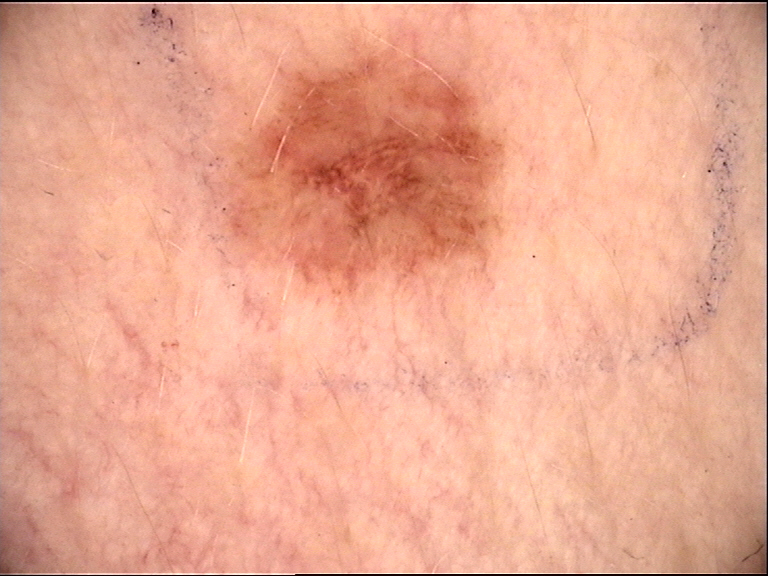image type — dermoscopy | diagnosis — dysplastic junctional nevus (expert consensus).